A dermoscopic view of a skin lesion; a male patient in their mid-70s — 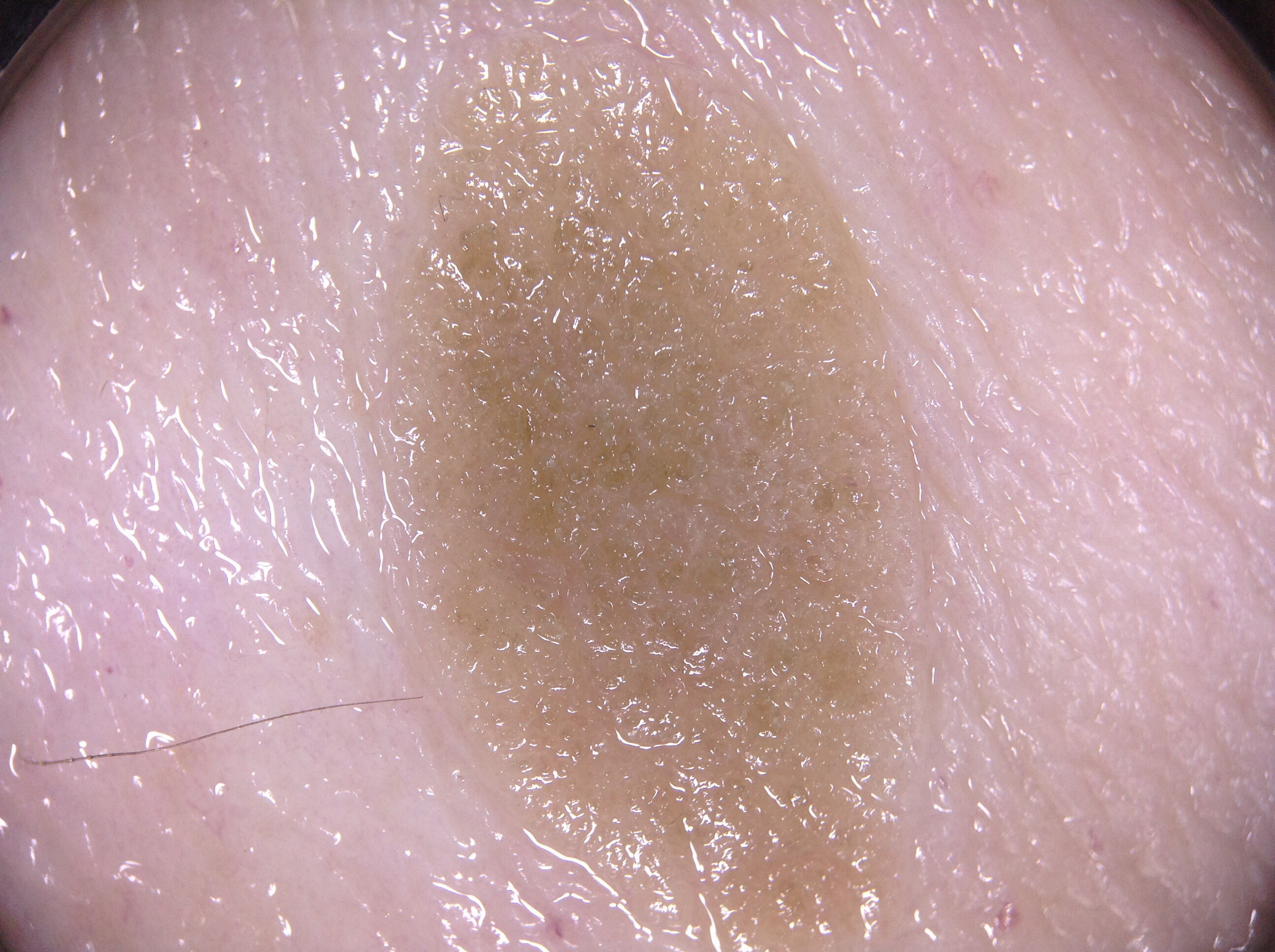Q: Which dermoscopic features are absent?
A: milia-like cysts, pigment network, negative network, and streaks
Q: What is the lesion's bounding box?
A: [357,11,946,947]
Q: How much of the field does the lesion occupy?
A: large
Q: What did the assessment conclude?
A: a seborrheic keratosis, a non-melanocytic (keratinocytic) lesion